Dermoscopy of a skin lesion: 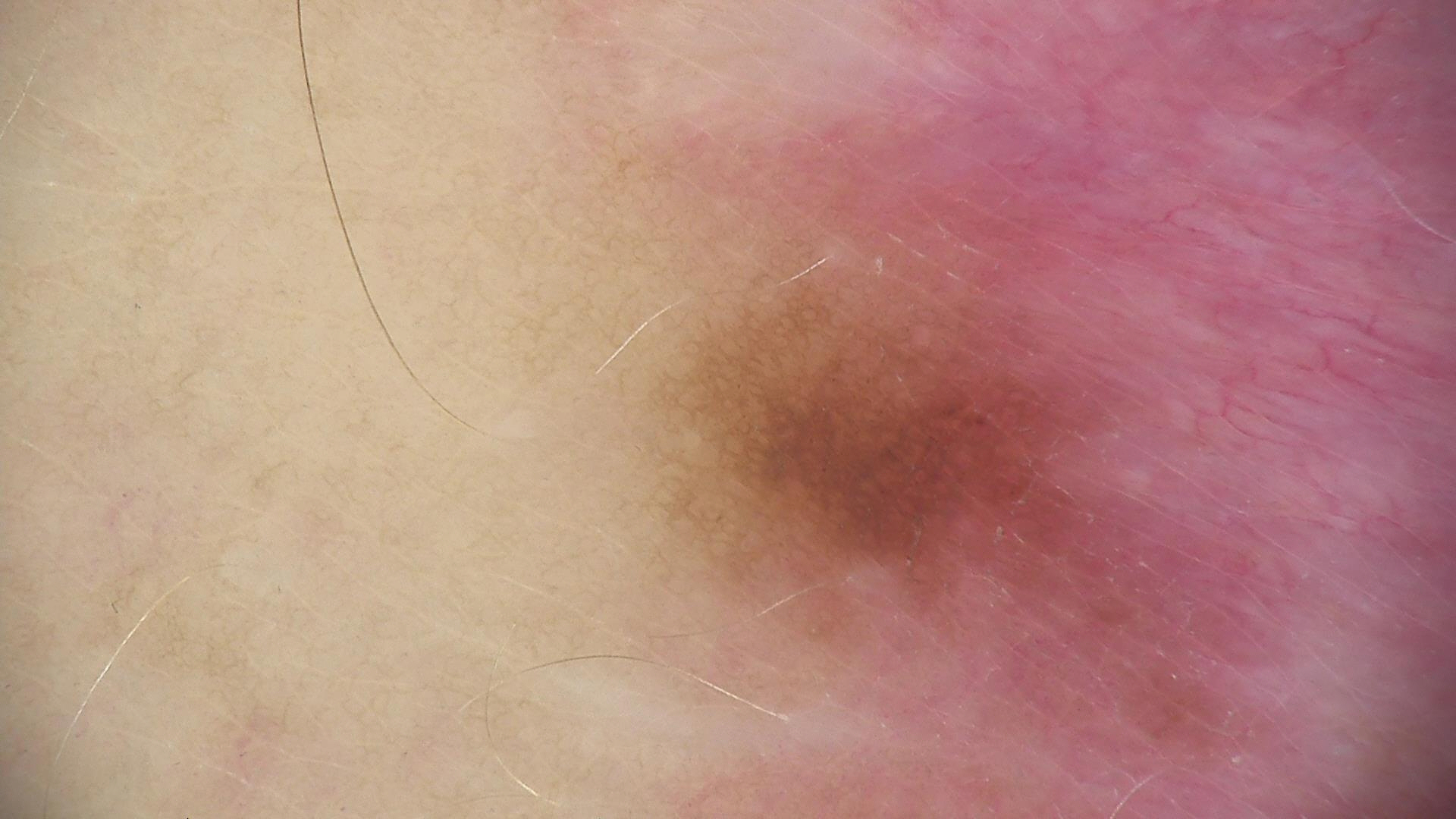- label: junctional nevus (expert consensus)